Close-up view, the contributor is a female aged 18–29, located on the arm.
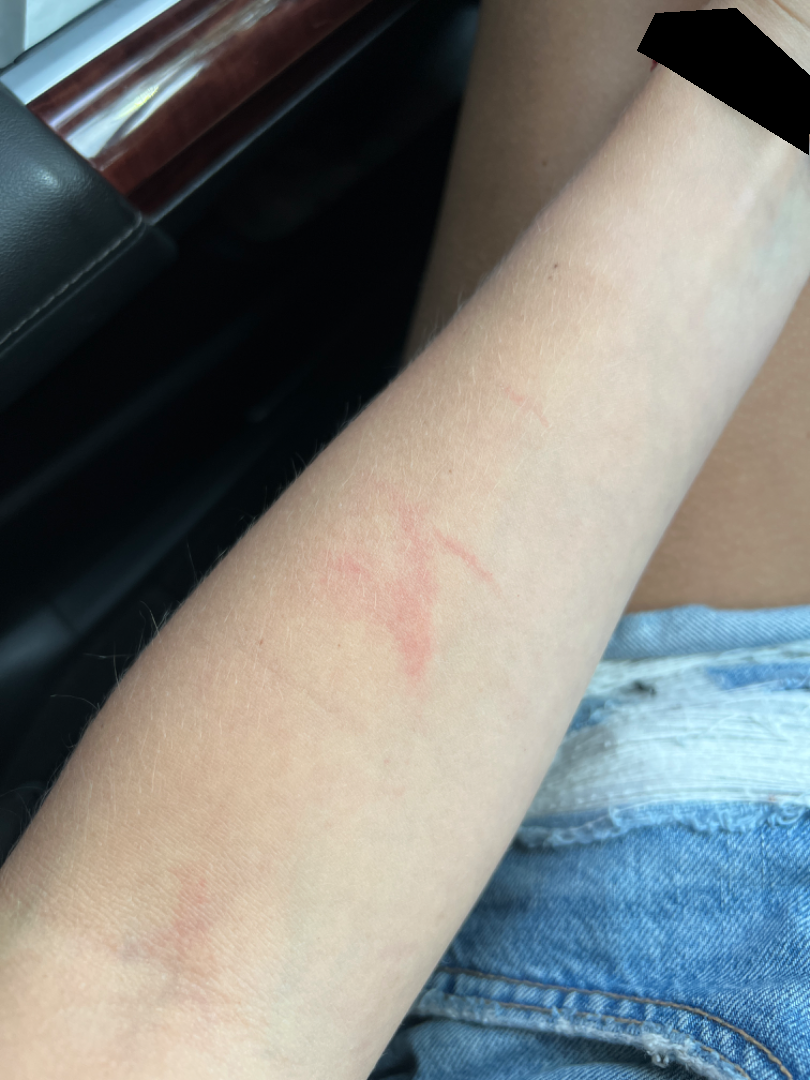Present for about one day. The patient reported no relevant symptoms from the lesion. The patient considered this a rash. Texture is reported as flat. Reviewed remotely by one dermatologist: the differential is split between Acute dermatitis, NOS and Irritant Contact Dermatitis.